A contact-polarized dermoscopy image of a skin lesion.
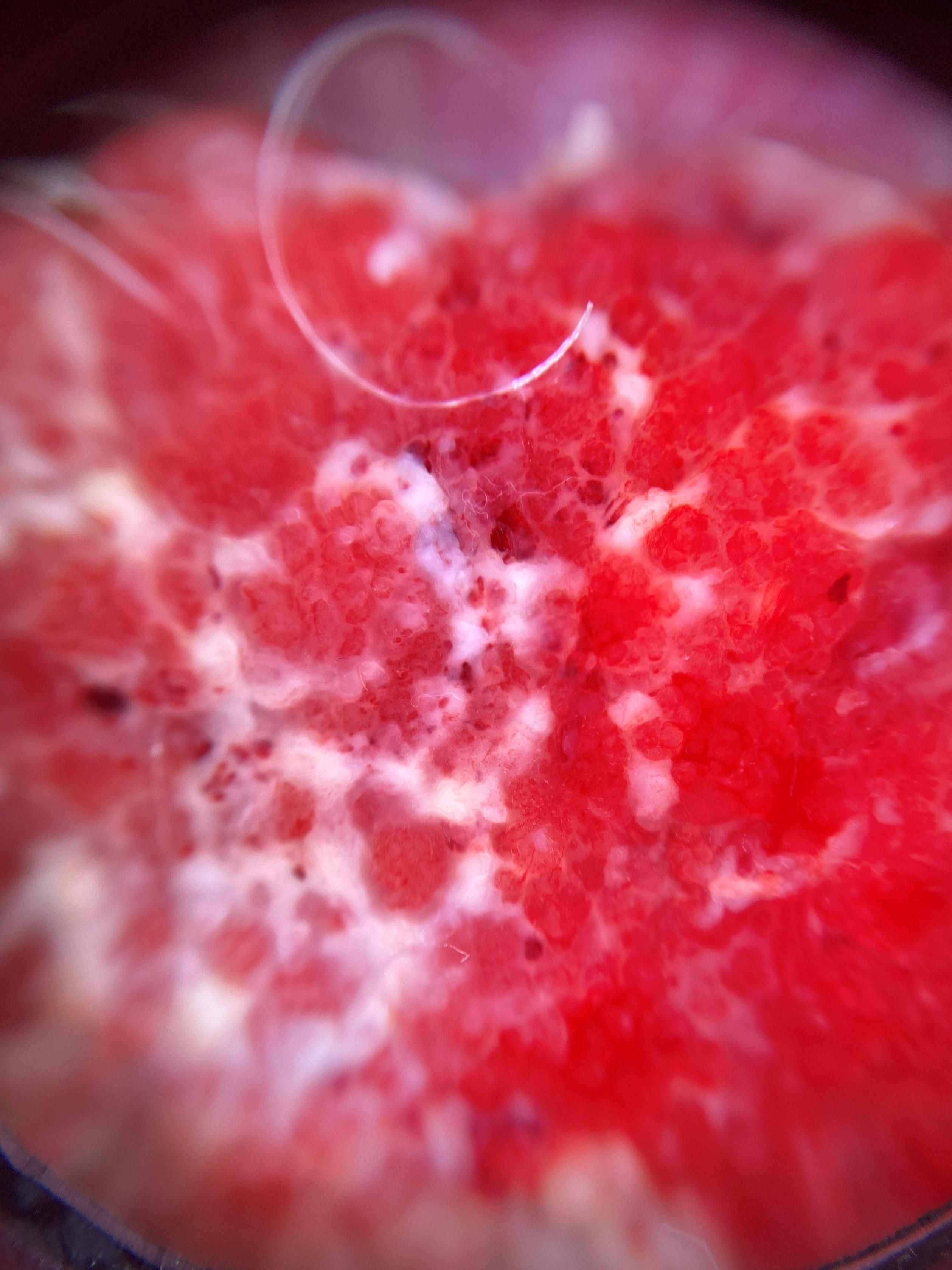The lesion was found on the head or neck. Confirmed on histopathology as a squamous cell carcinoma.